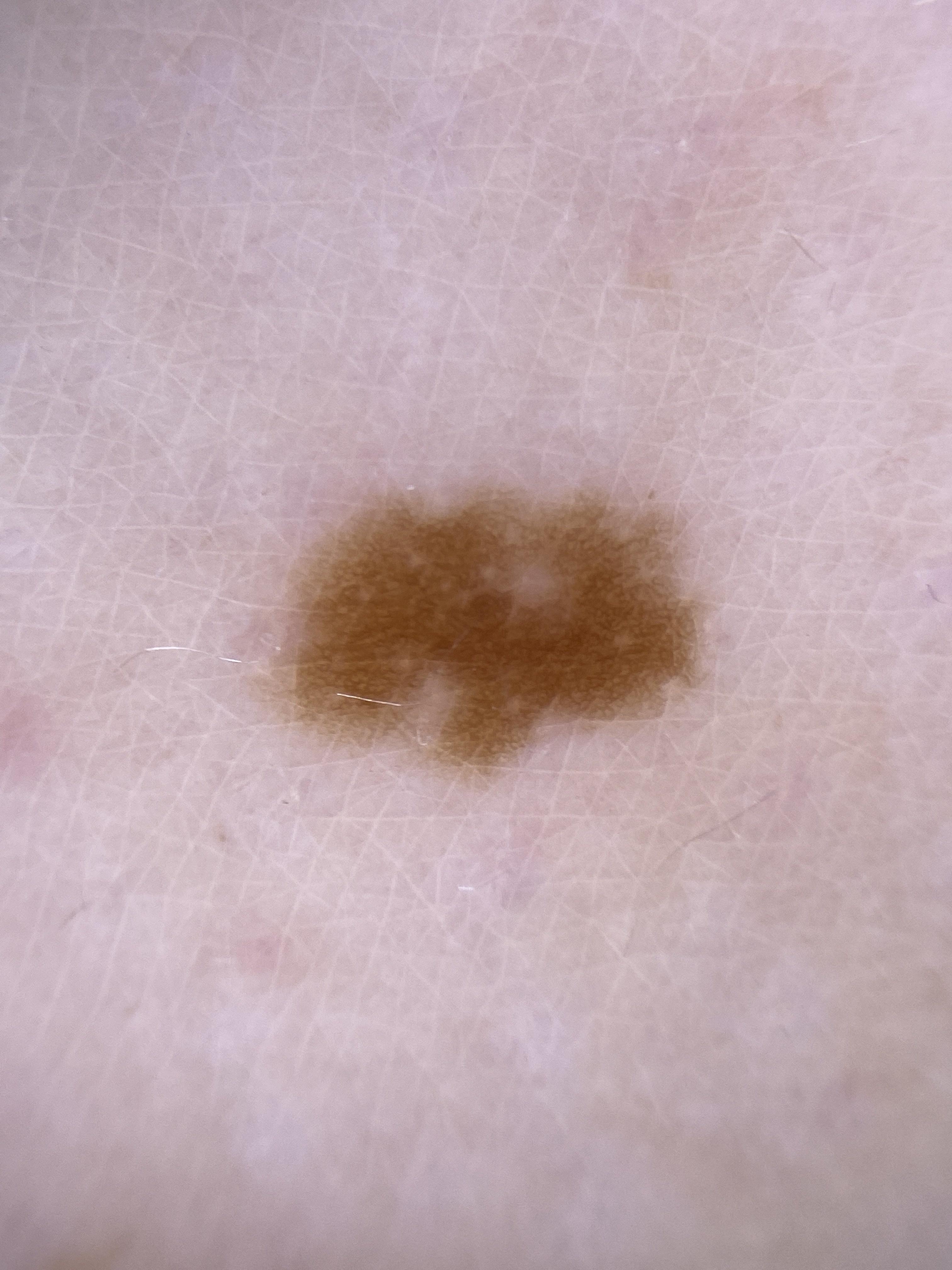Case summary:
The chart documents a previous melanoma. A dermatoscopic image of a skin lesion. A female patient aged 23-27. Recorded as FST II. The lesion is located on a lower extremity.
Impression:
Clinically diagnosed as a melanocytic lesion — a nevus.